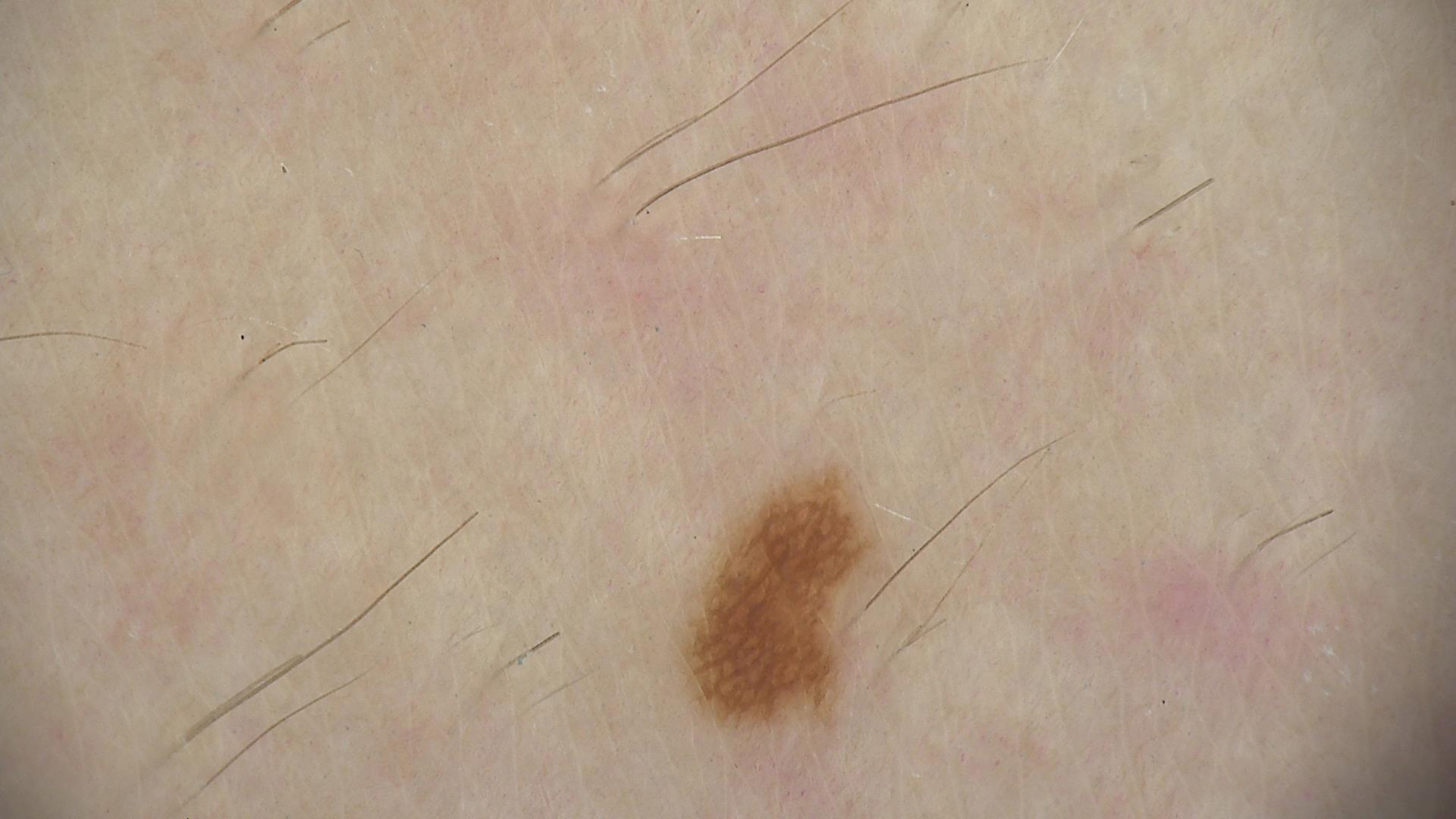A dermatoscopic image of a skin lesion. Labeled as a junctional nevus.